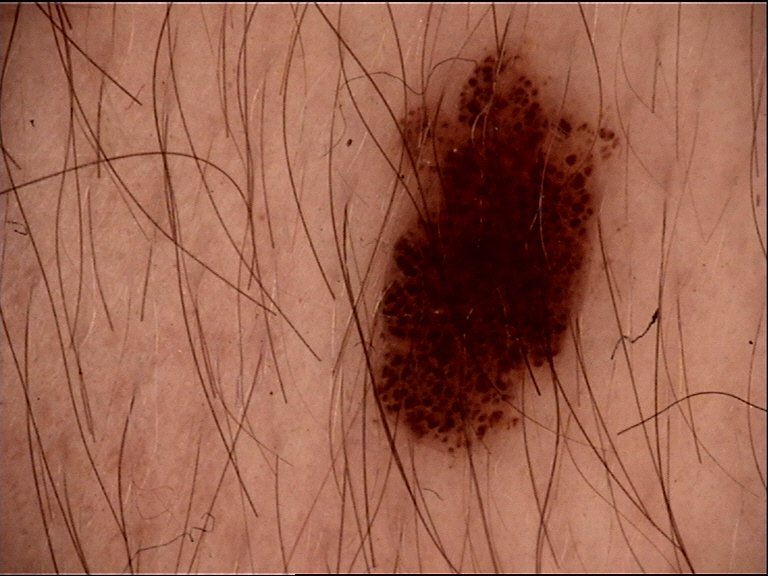image: dermatoscopy
diagnosis:
  name: dysplastic compound nevus
  code: cd
  malignancy: benign
  super_class: melanocytic
  confirmation: expert consensus